Close-up view: 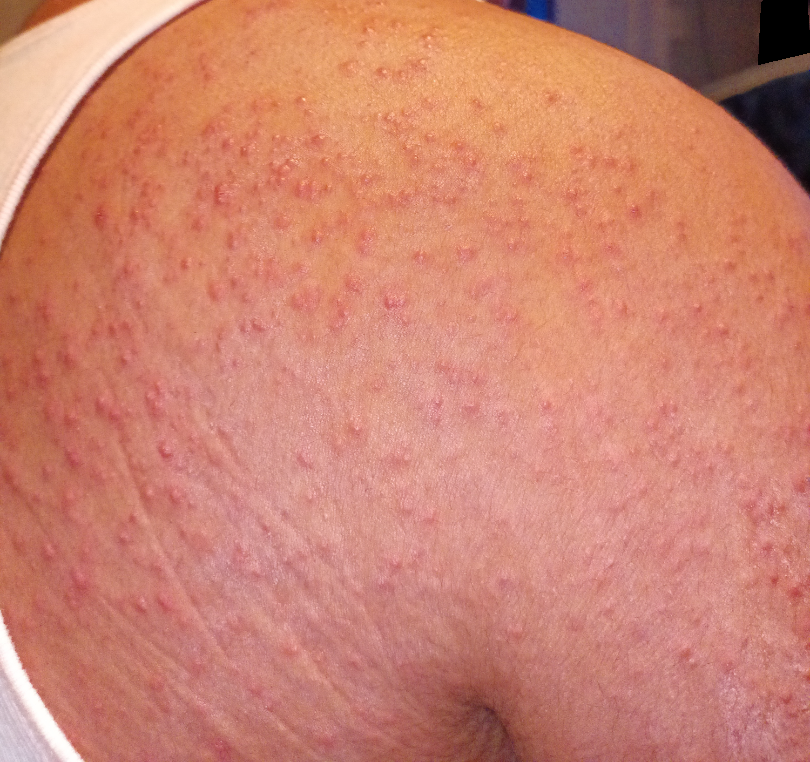One reviewing dermatologist: the favored diagnosis is Miliaria; possibly Acne; also consider Keratosis pilaris.